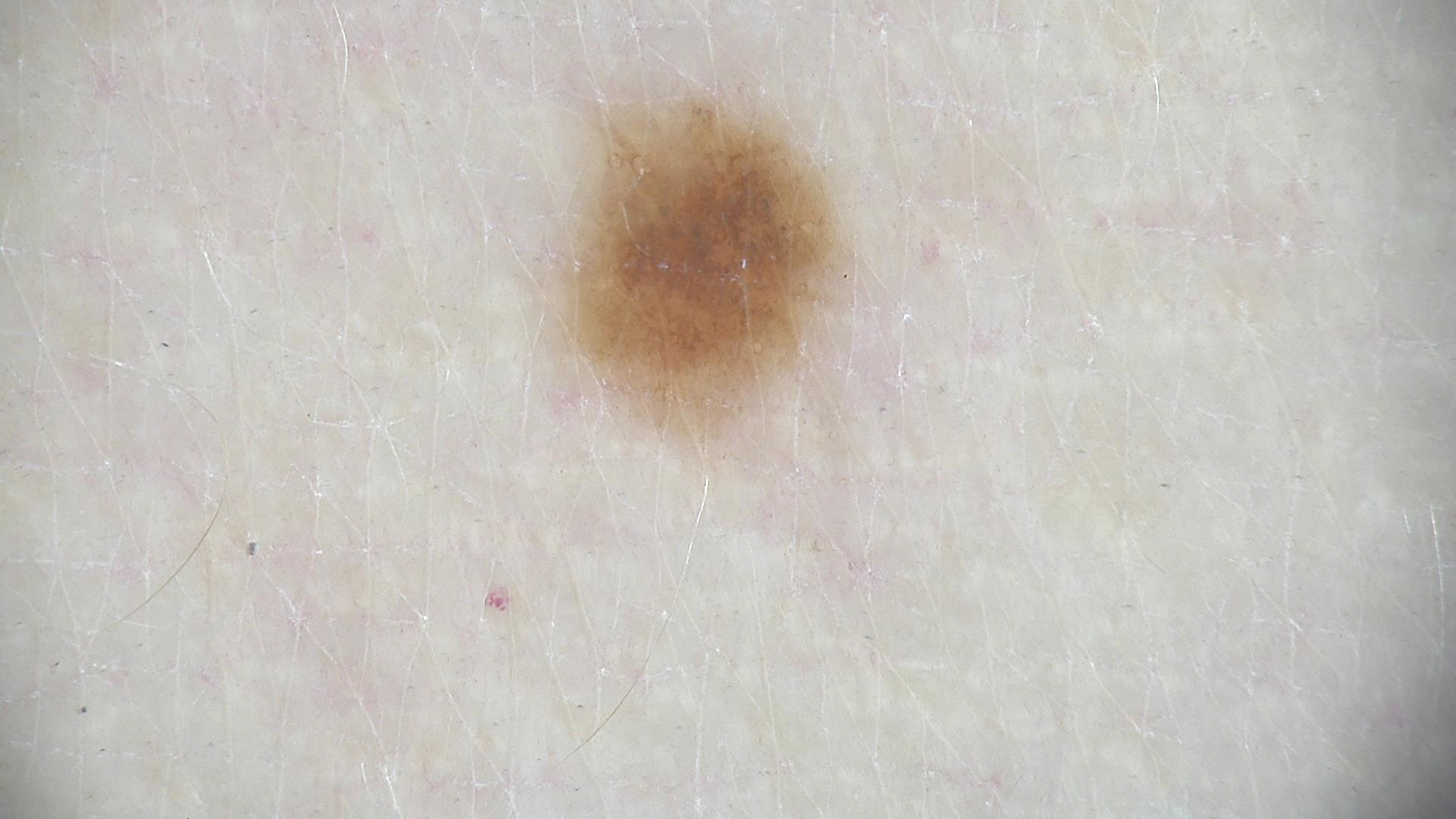Case:
• diagnostic label: junctional nevus (expert consensus)